This image was taken at an angle.
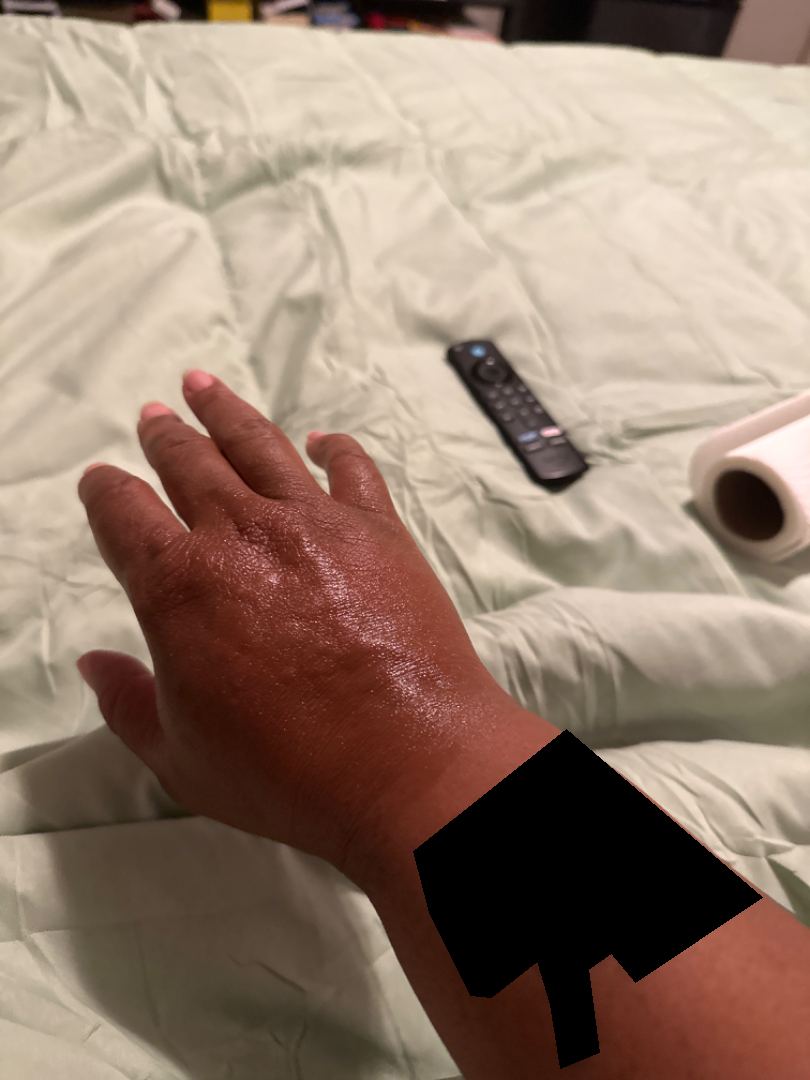| feature | finding |
|---|---|
| assessment | the impression on review was Urticaria |